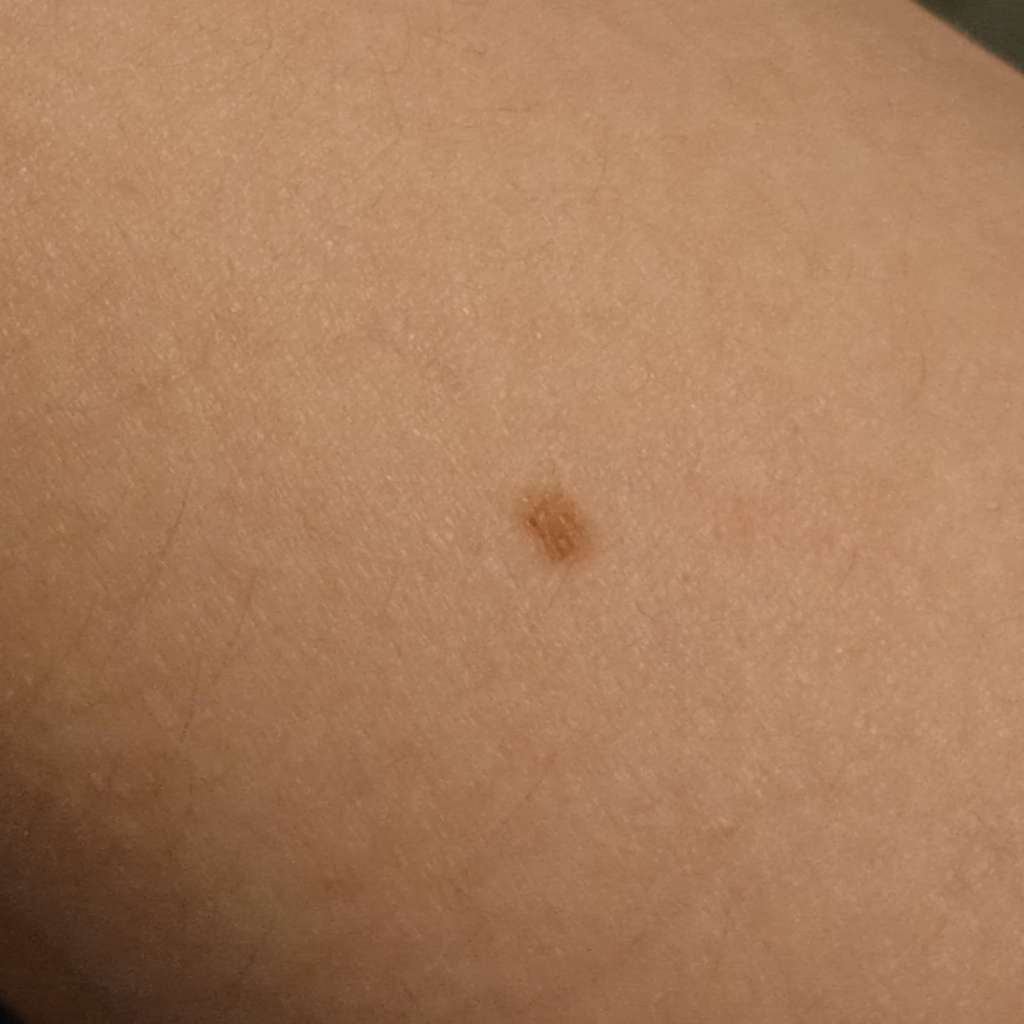Few moles overall by the patient's own estimate. Imaged for a research study, with no referral diagnosis recorded. A male patient aged 15. The patient says their skin tans without first burning. A clinical close-up of a skin lesion. The lesion is located on an arm. The diagnostic impression was a melanocytic nevus.